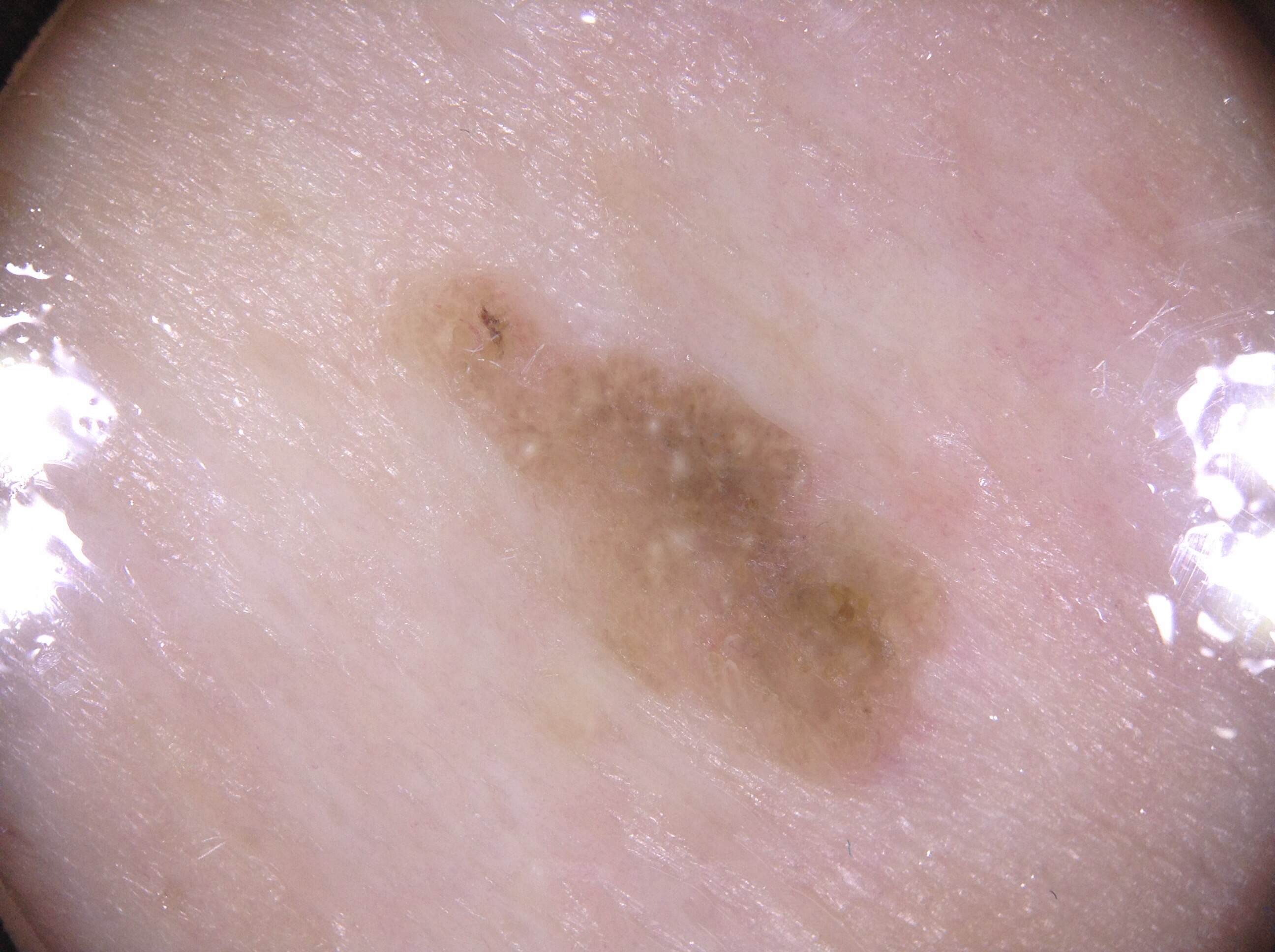{"image": {"modality": "dermoscopy"}, "patient": {"sex": "male", "age_approx": 75}, "lesion_location": {"bbox_xyxy": [385, 266, 974, 804]}, "dermoscopic_features": {"present": ["milia-like cysts"], "absent": ["pigment network", "negative network", "streaks"]}, "diagnosis": {"name": "seborrheic keratosis", "malignancy": "benign", "lineage": "keratinocytic", "provenance": "clinical"}}